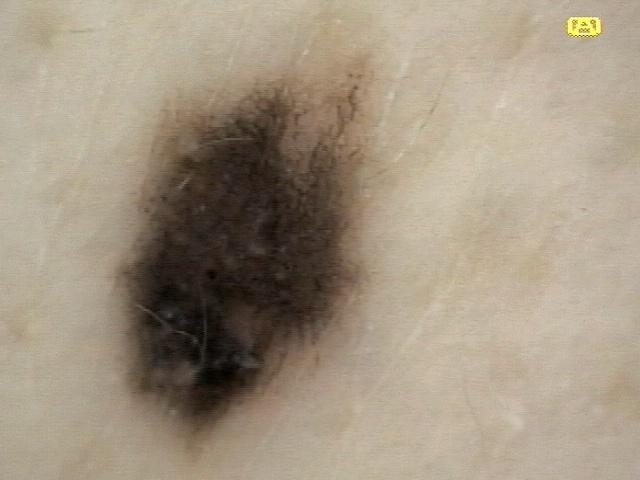A female subject aged around 45. The patient is Fitzpatrick phototype II. The lesion involves the anterior trunk. The biopsy diagnosis was a benign lesion — a nevus.